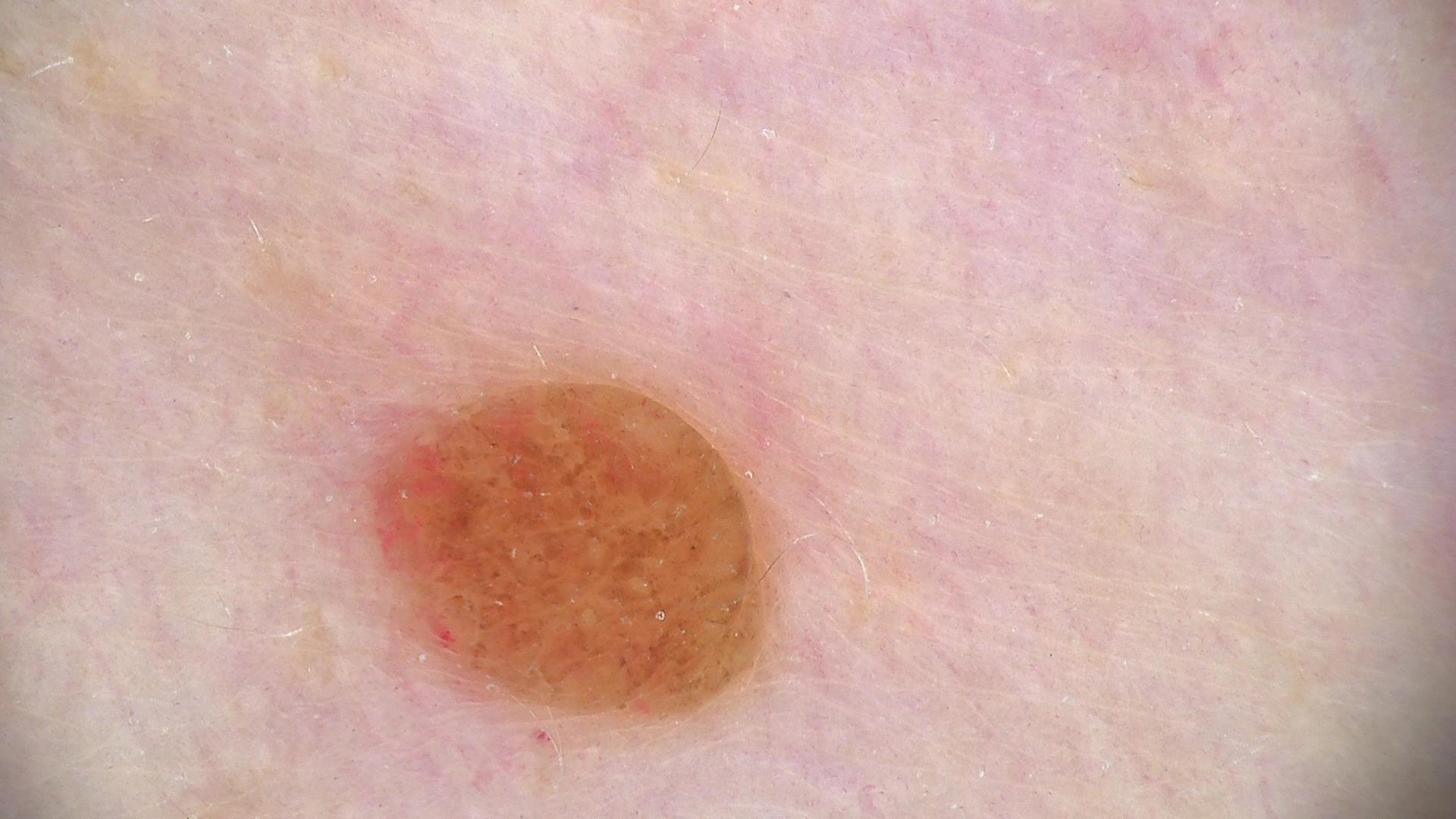A dermoscopic image of a skin lesion. Consistent with a compound nevus.